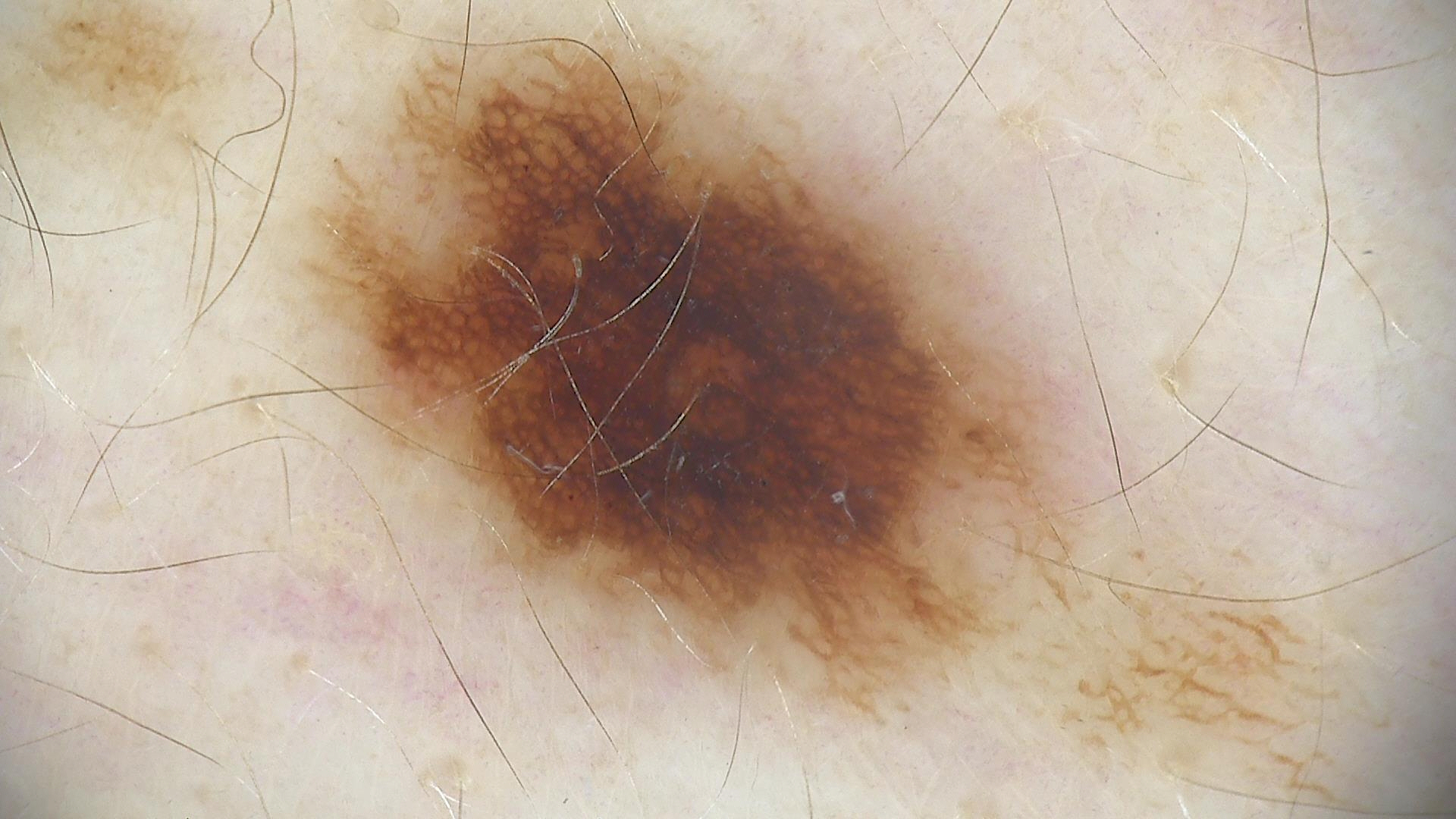Classified as a dysplastic junctional nevus.